A dermatoscopic image of a skin lesion: 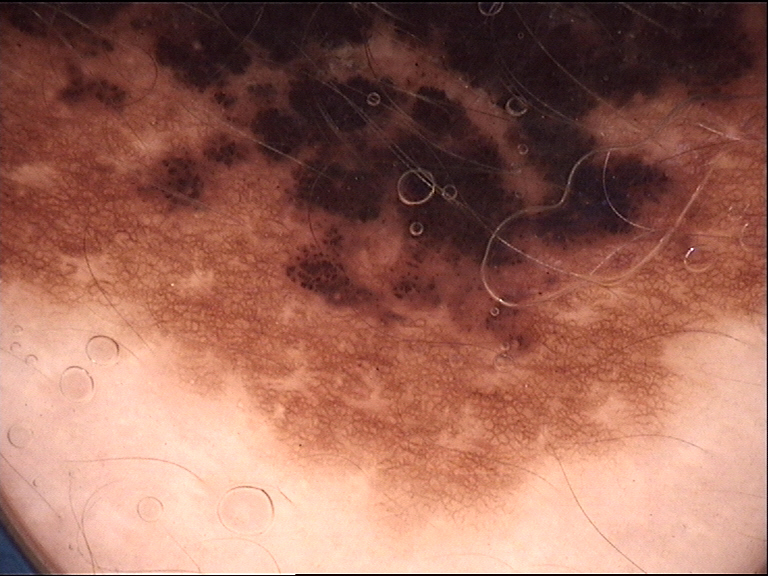The morphology is that of a banal lesion.
Consistent with a congenital compound nevus.